A dermoscopic close-up of a skin lesion.
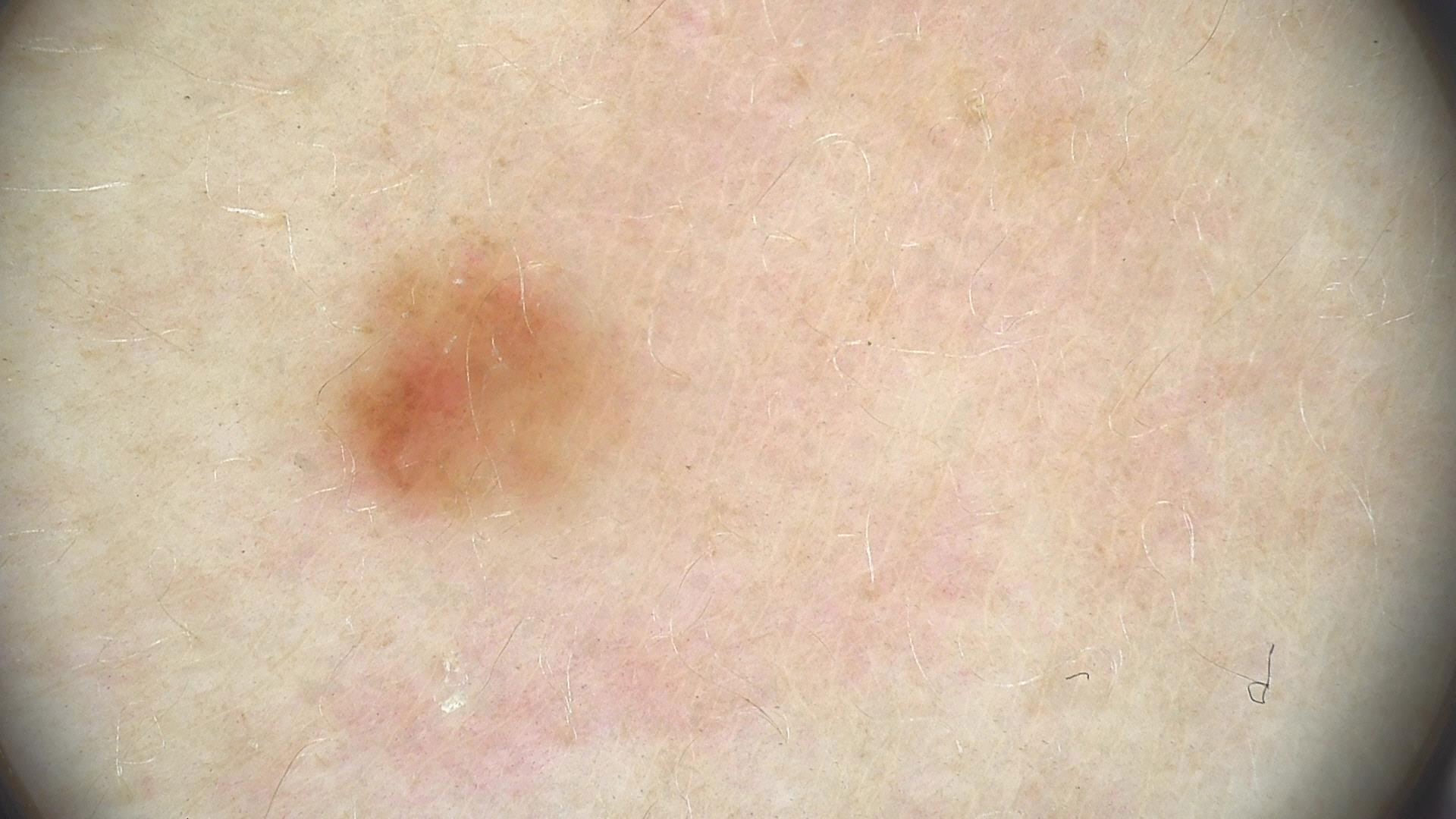<dermoscopy>
  <diagnosis>
    <name>dysplastic junctional nevus</name>
    <code>jd</code>
    <malignancy>benign</malignancy>
    <super_class>melanocytic</super_class>
    <confirmation>expert consensus</confirmation>
  </diagnosis>
</dermoscopy>